A dermatoscopic image of a skin lesion; a female patient, aged approximately 50.
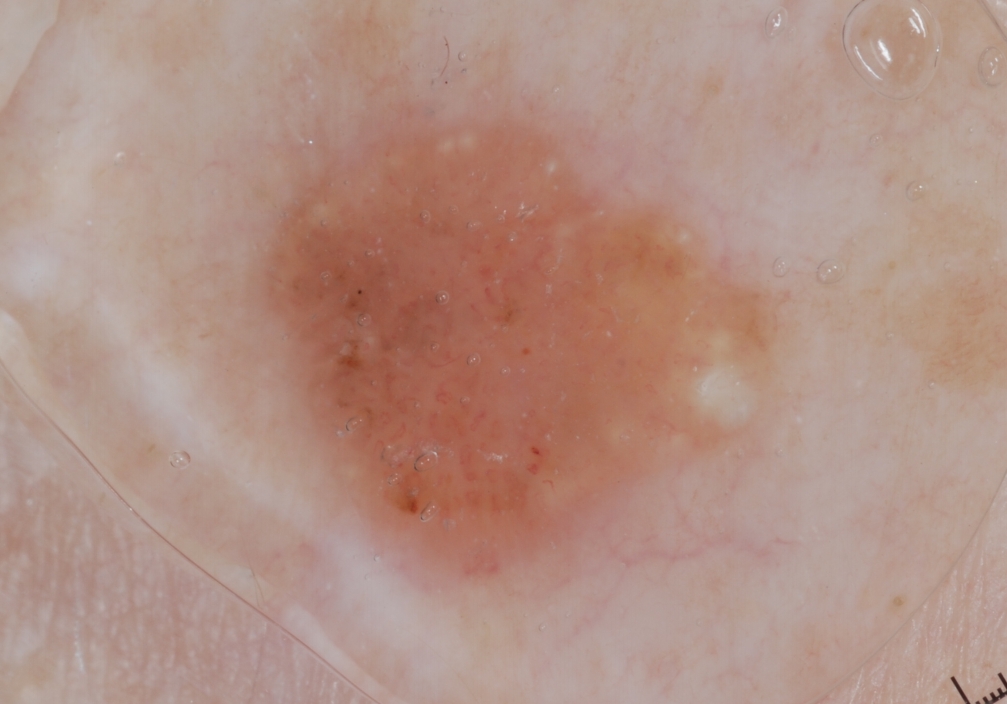Image and clinical context:
The lesion is bounded by left=214, top=77, right=798, bottom=658. Dermoscopy demonstrates milia-like cysts, with no negative network, pigment network, or streaks.
Impression:
Clinically diagnosed as a seborrheic keratosis.